This image was taken at an angle. The contributor is 30–39, male:
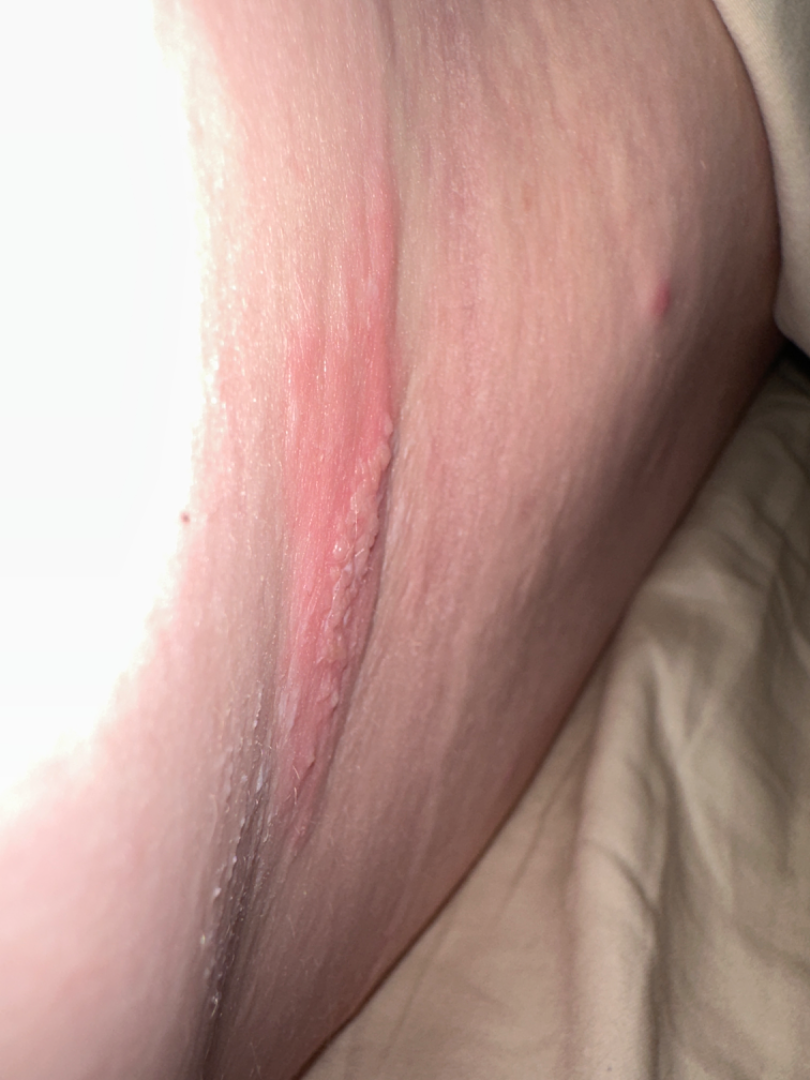The leading impression is Herpes Simplex; with consideration of Herpes Zoster.